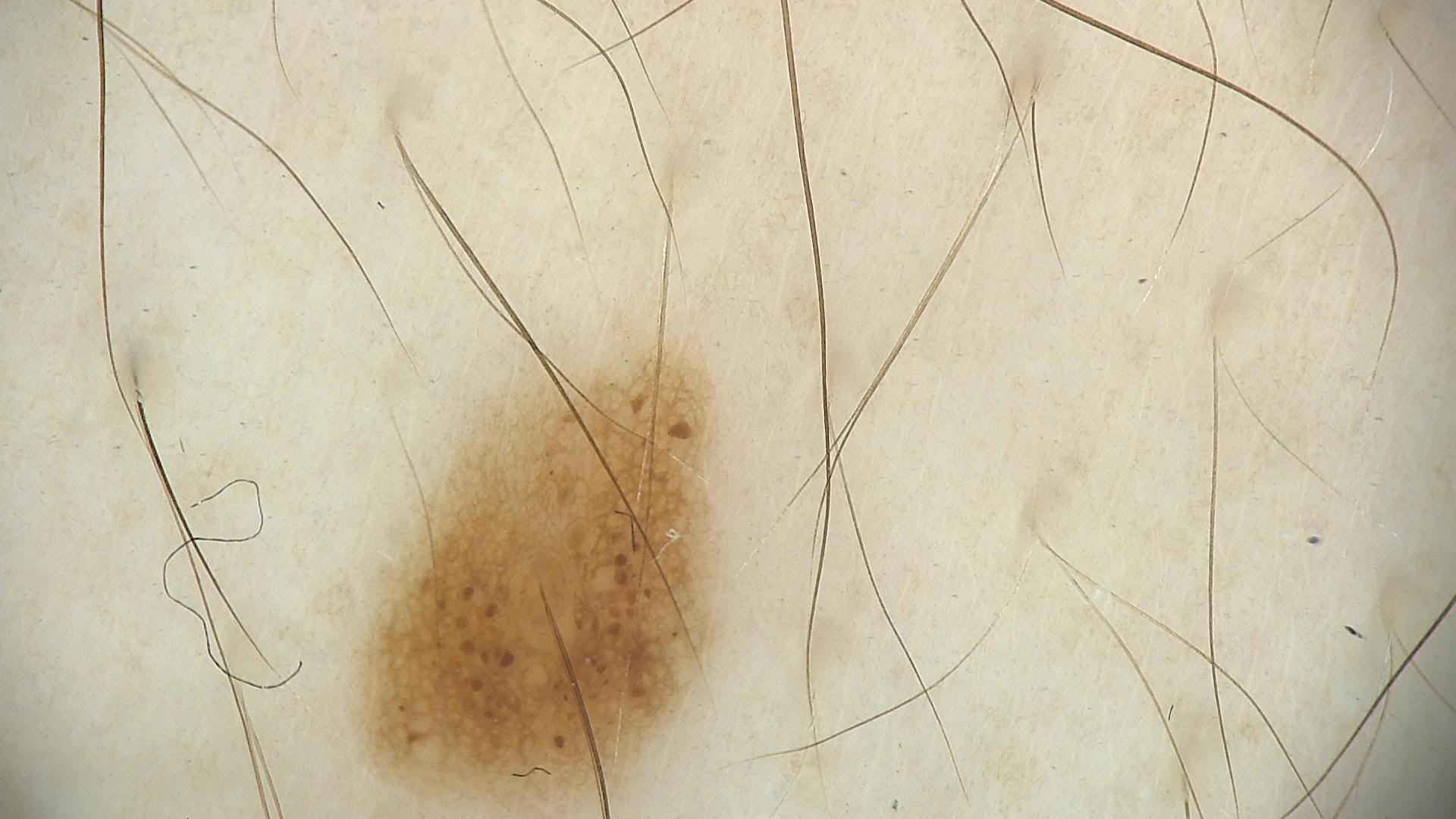* modality: dermoscopy
* assessment: dysplastic junctional nevus (expert consensus)